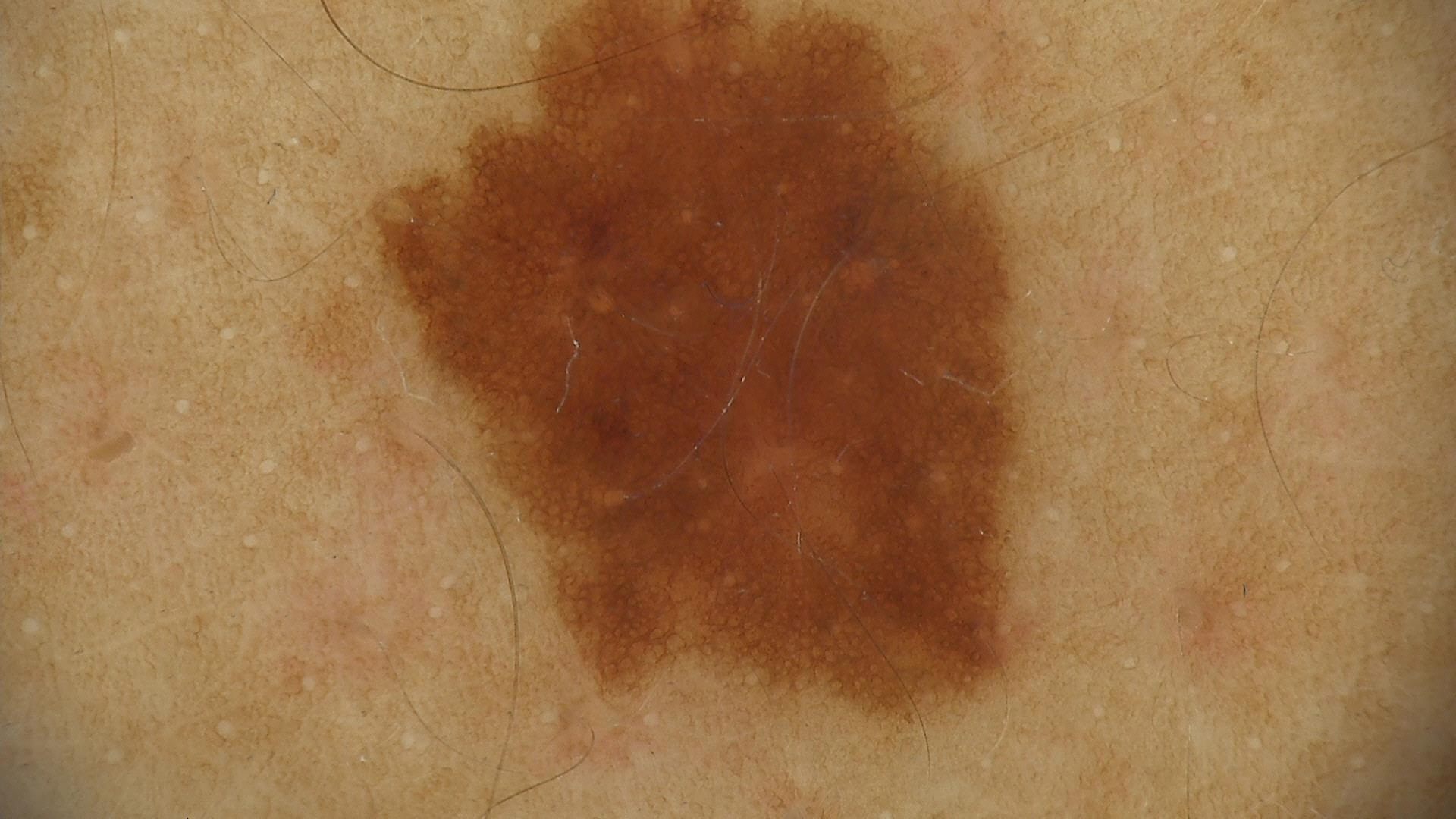imaging: dermoscopy
assessment: dysplastic junctional nevus (expert consensus)